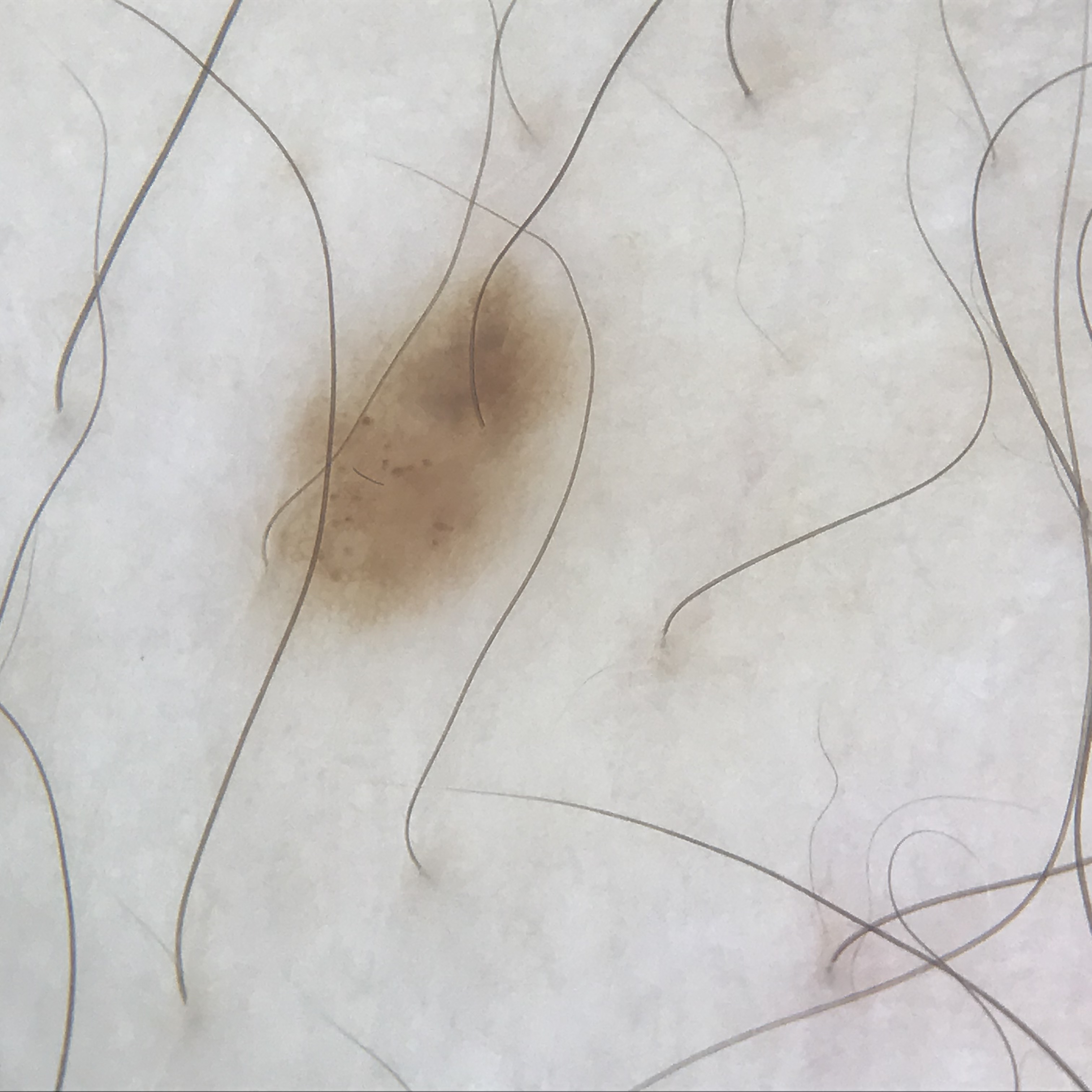modality: dermatoscopy | label: dysplastic junctional nevus (expert consensus).